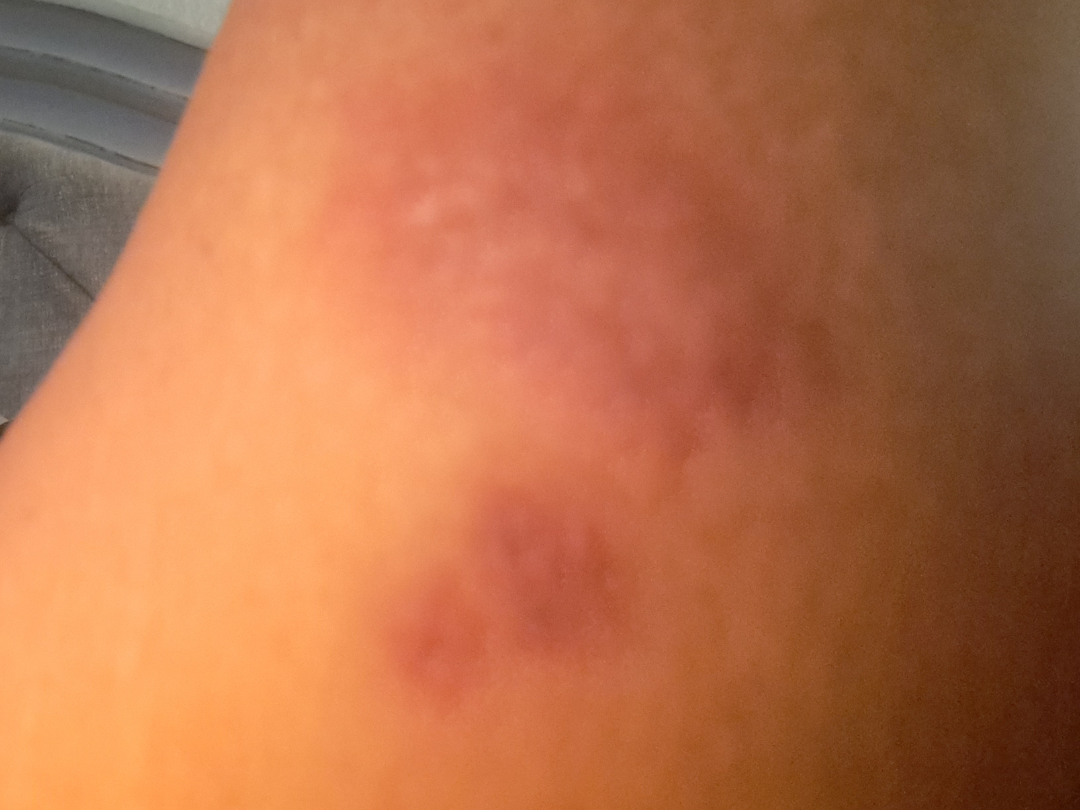The reviewer was unable to grade this case for skin condition. A close-up photograph.